A close-up photograph.
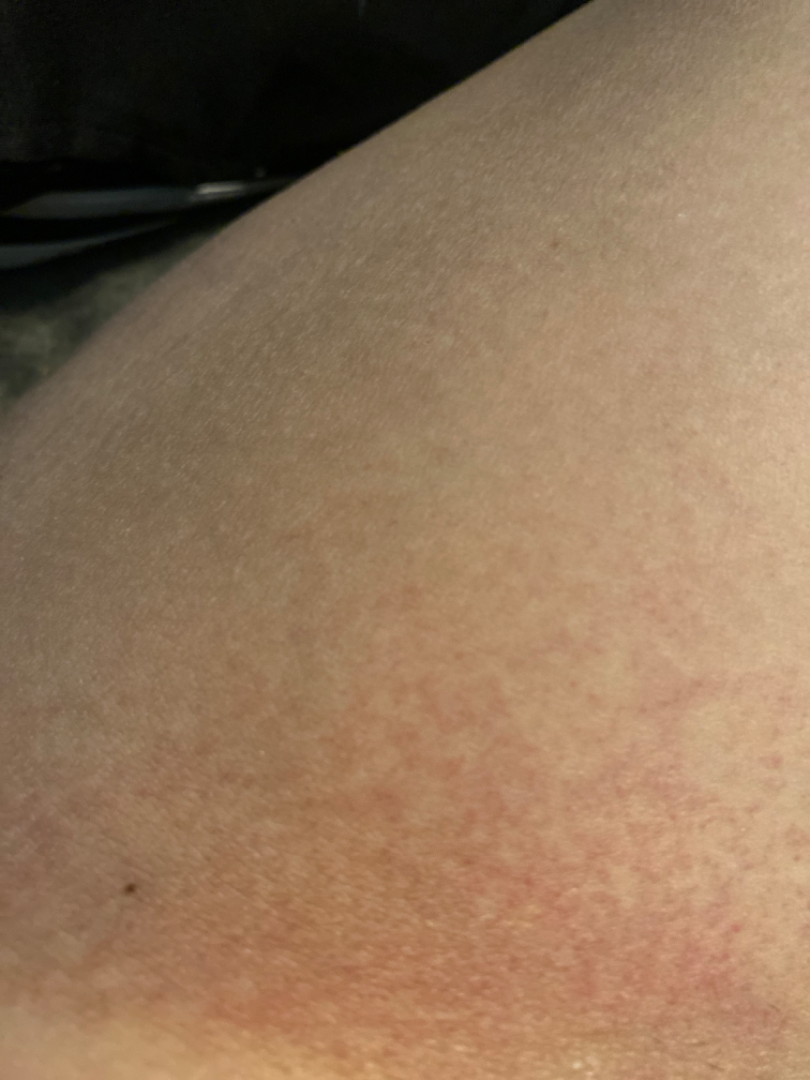<summary>
<differential>
  <tied_lead>Hypersensitivity, Allergic Contact Dermatitis, Irritant Contact Dermatitis</tied_lead>
</differential>
</summary>